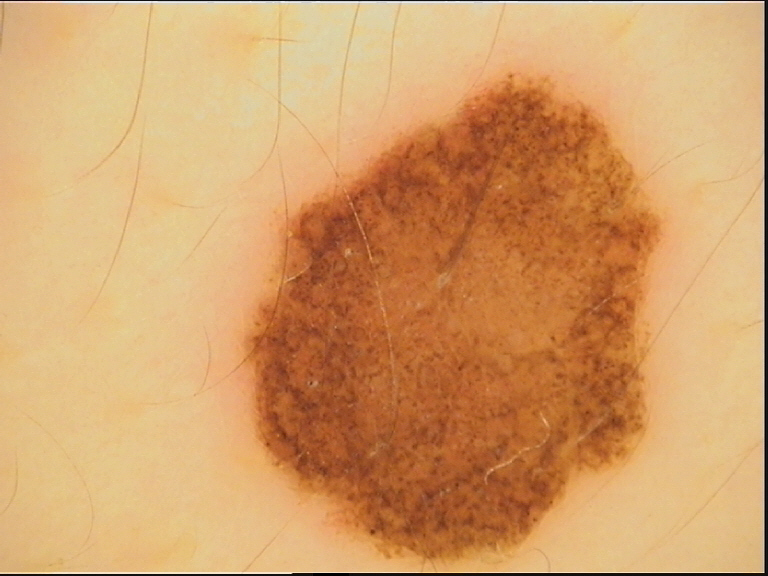A skin lesion imaged with a dermatoscope. Diagnosed as a benign lesion — a dysplastic compound nevus.